A dermatoscopic image of a skin lesion:
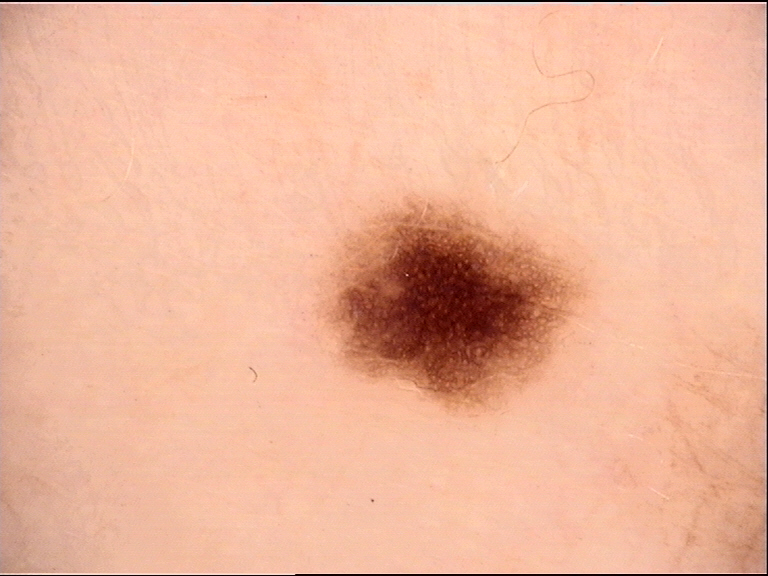category: banal, assessment: junctional nevus (expert consensus).